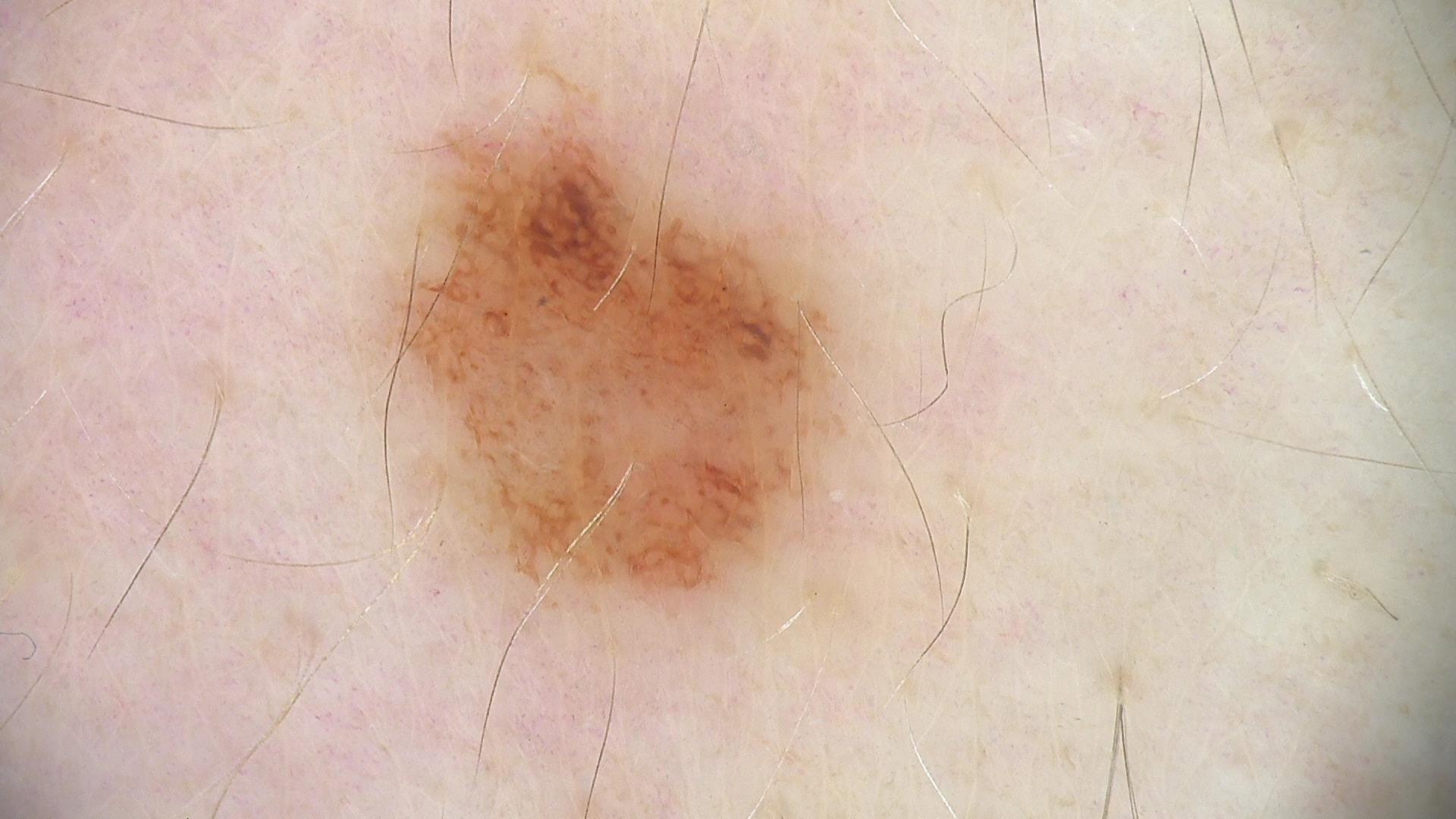Classified as a dysplastic junctional nevus.